This image was taken at a distance. Female contributor, age 70–79. Located on the front of the torso and leg.
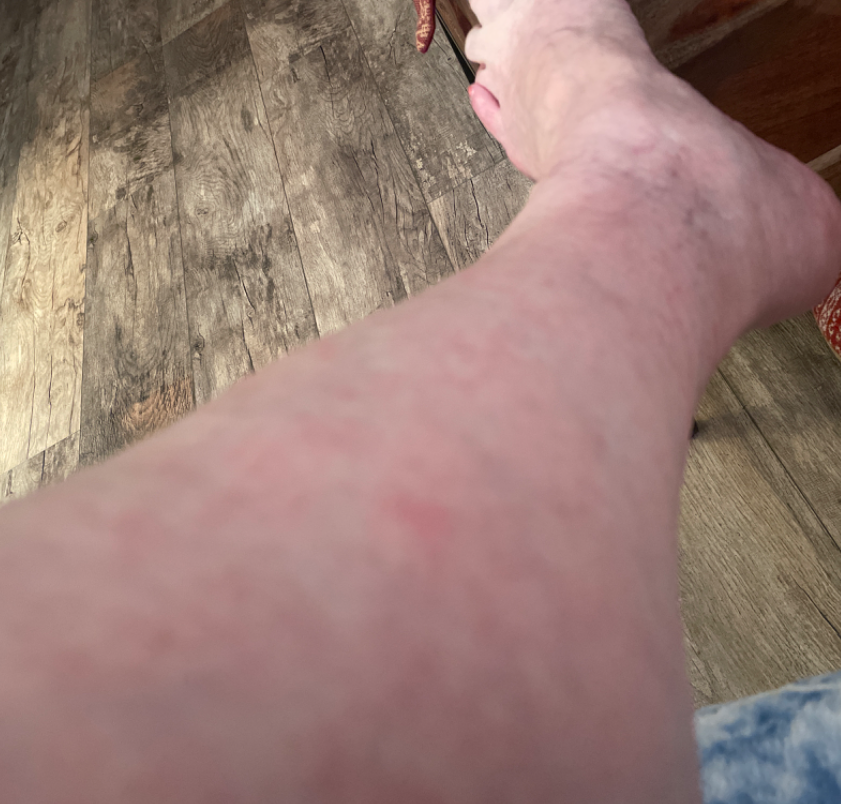associated systemic symptoms = none reported, surface texture = raised or bumpy, onset = about one day, patient describes the issue as = a rash, clinical impression = most consistent with Drug Rash; also raised was Viral Exanthem; a remote consideration is Urticaria.